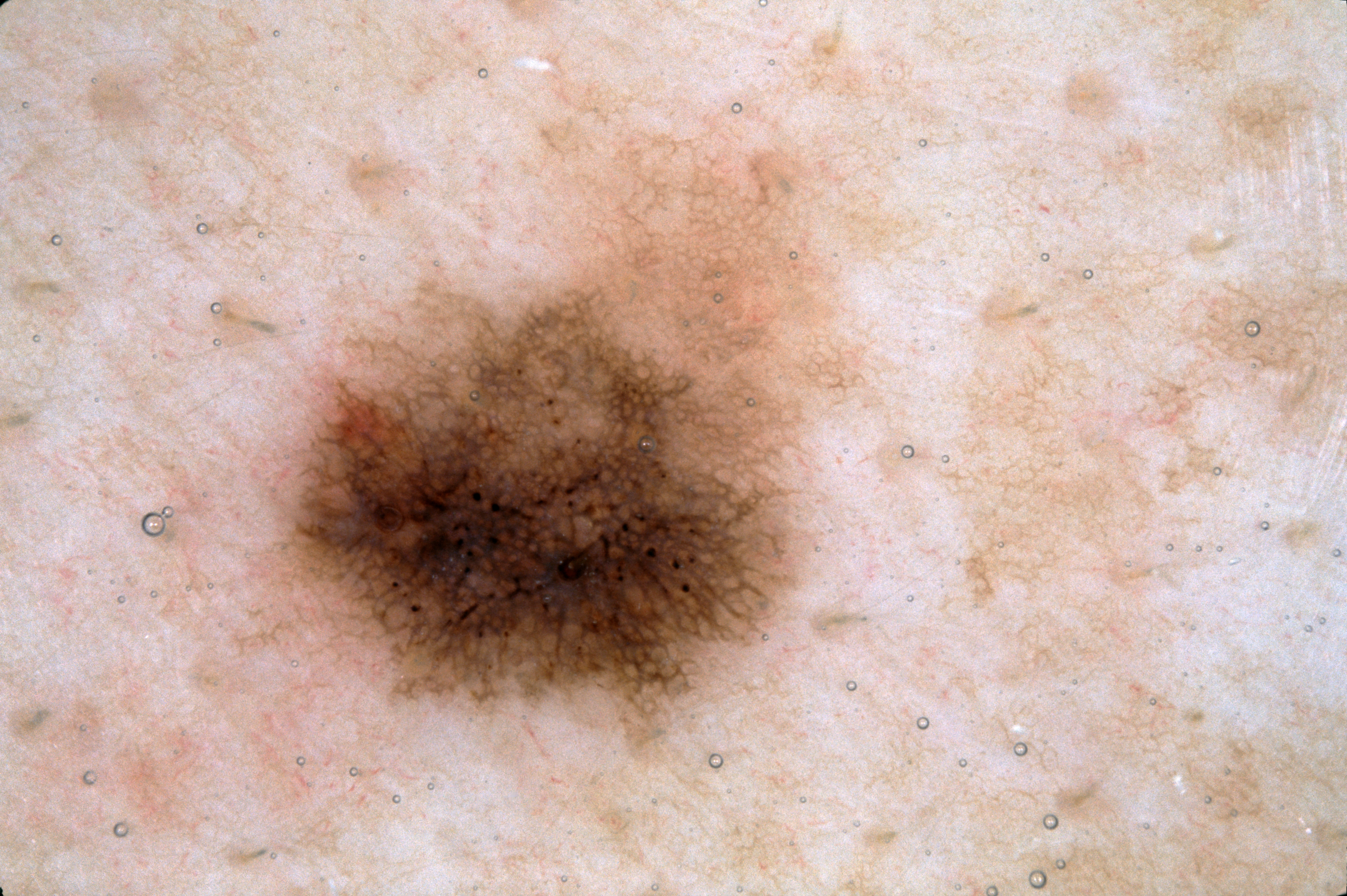Case summary: A female patient about 45 years old. A dermoscopic close-up of a skin lesion. As (left, top, right, bottom), the lesion is located at 226, 131, 866, 772. The lesion covers approximately 21% of the dermoscopic field. The dermoscopic pattern shows pigment network. Assessment: The clinical diagnosis was a melanocytic nevus.